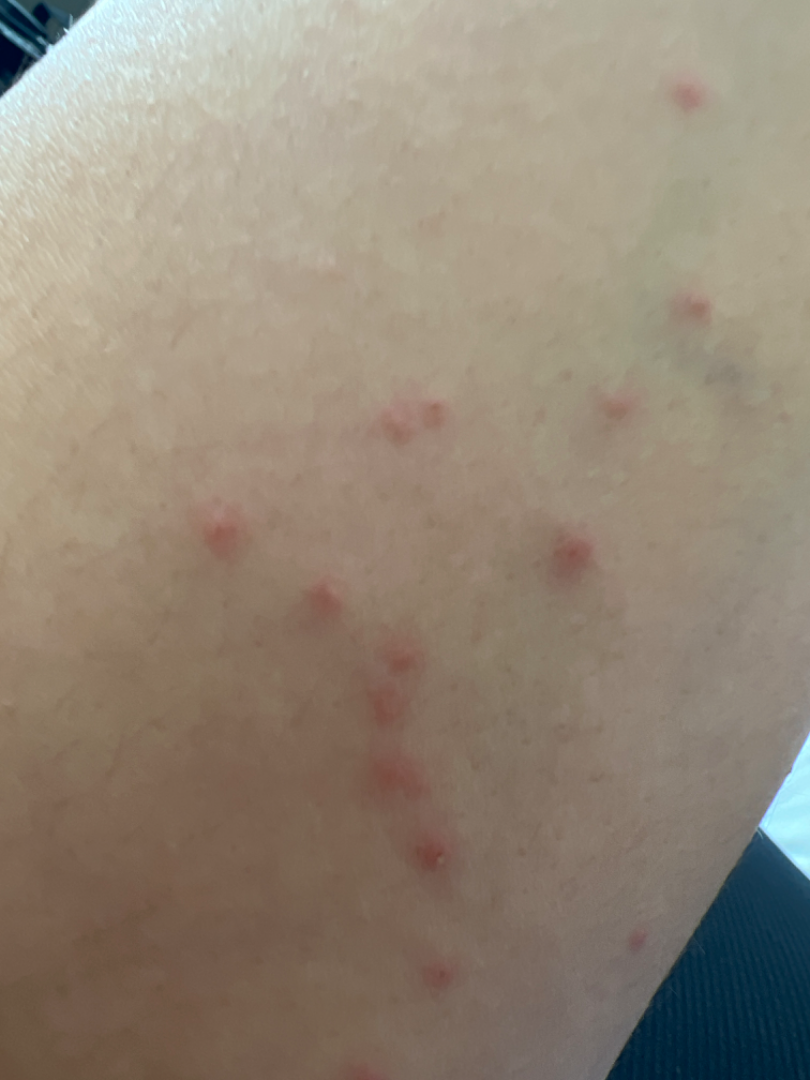Clinical context: Skin tone: Fitzpatrick skin type III. Texture is reported as raised or bumpy. Located on the arm. The photograph is a close-up of the affected area. Reported lesion symptoms include itching. The condition has been present for less than one week. Assessment: Reviewed remotely by one dermatologist: the primary impression is Insect Bite; the differential also includes Hypersensitivity; less likely is Eczema.